This is a close-up image.
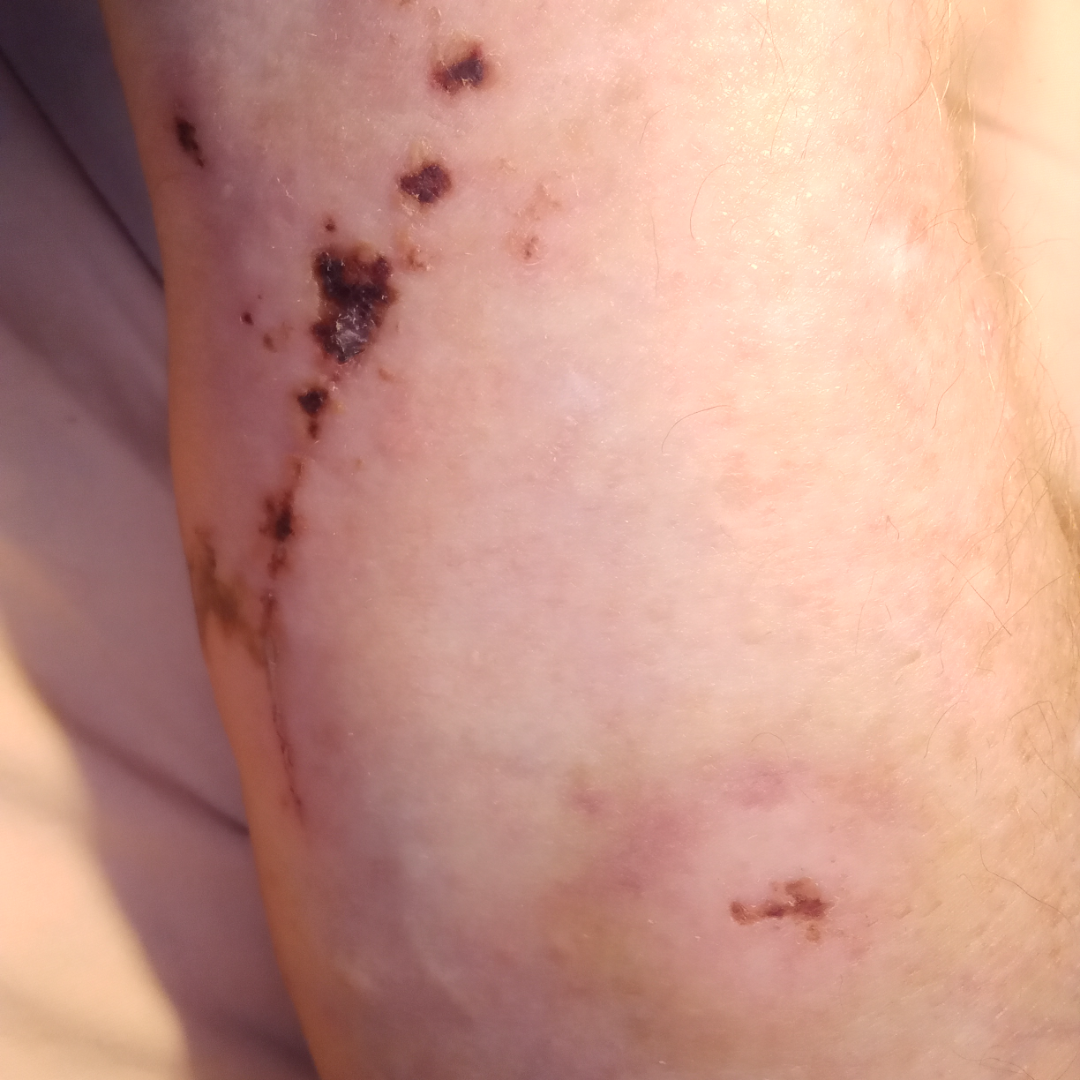Notes:
* assessment · indeterminate
* lesion texture · raised or bumpy
* skin tone · non-clinician graders estimated Monk Skin Tone 2–3